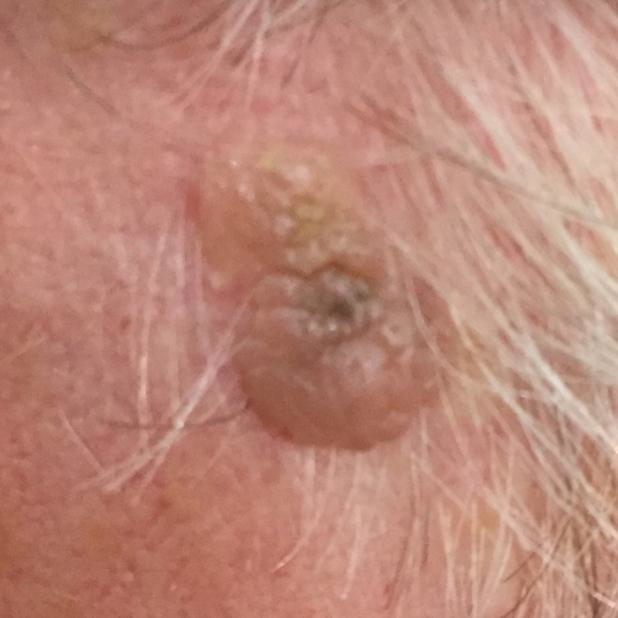modality: clinical photograph
region: the face
symptoms: growth, elevation
impression: seborrheic keratosis (clinical consensus)